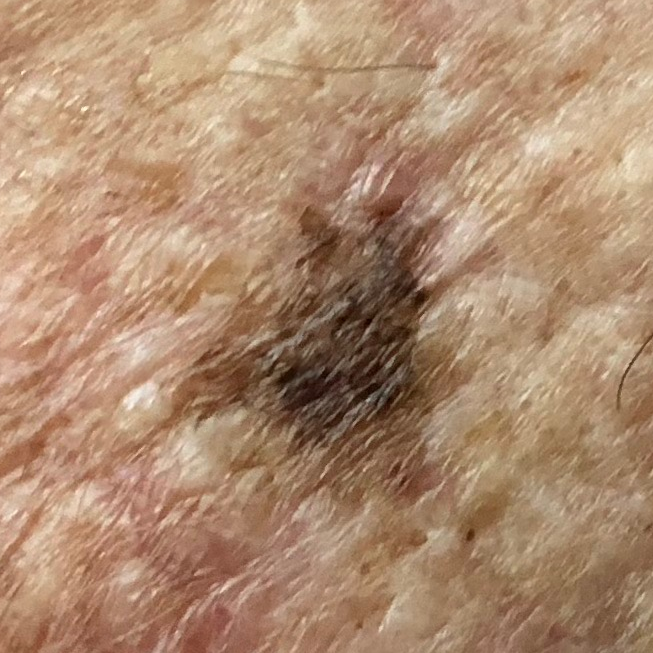Case:
* exposure history — prior skin cancer (patient or family)
* Fitzpatrick — II
* image type — clinical photo
* region — the chest
* pathology — melanoma (biopsy-proven)